Few moles overall by the patient's own estimate. A skin lesion imaged with a dermatoscope. The patient says their skin tans without first burning. A female patient 68 years old: 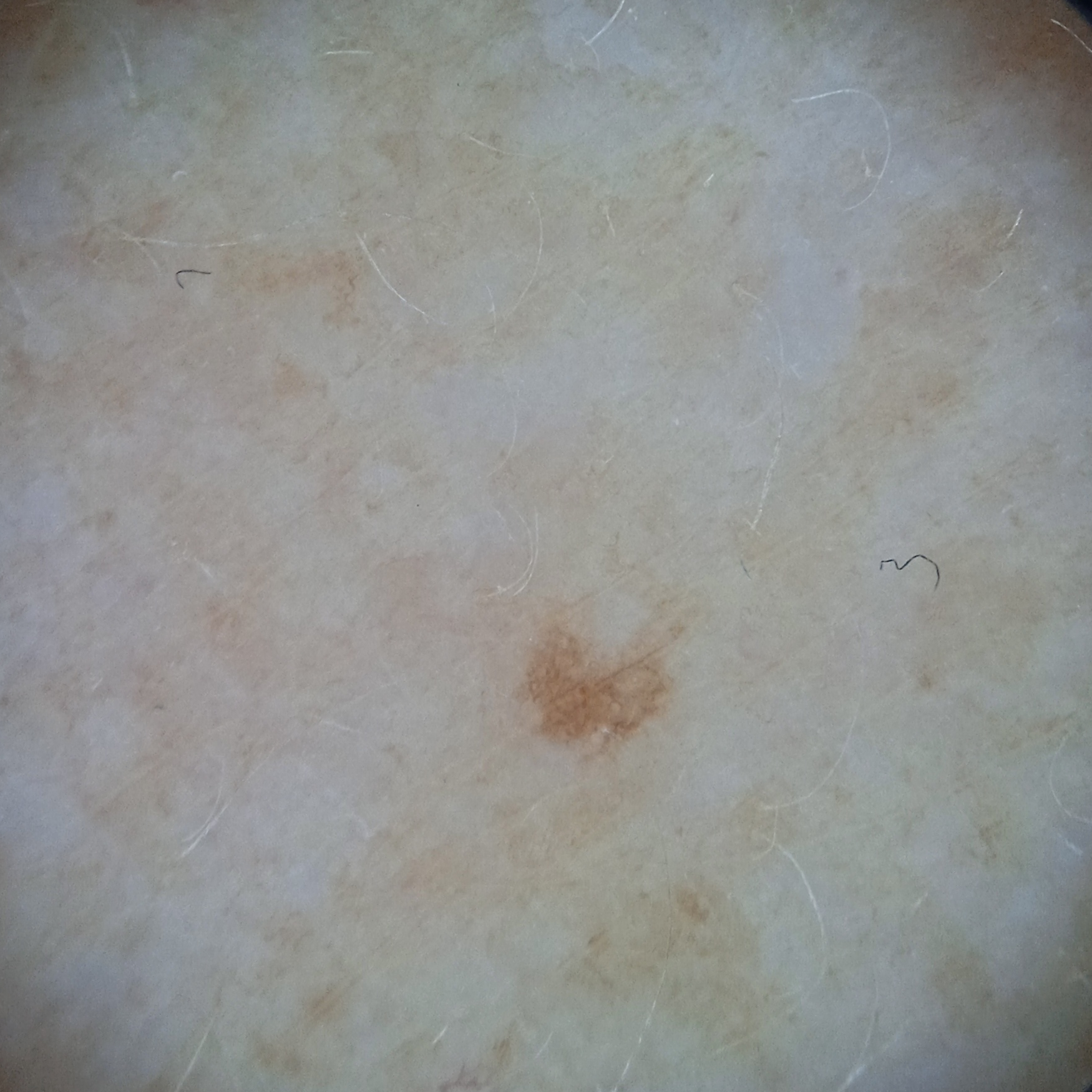The lesion involves an arm. The lesion is about 1.7 mm across. Dermatologist review favored a melanocytic nevus.